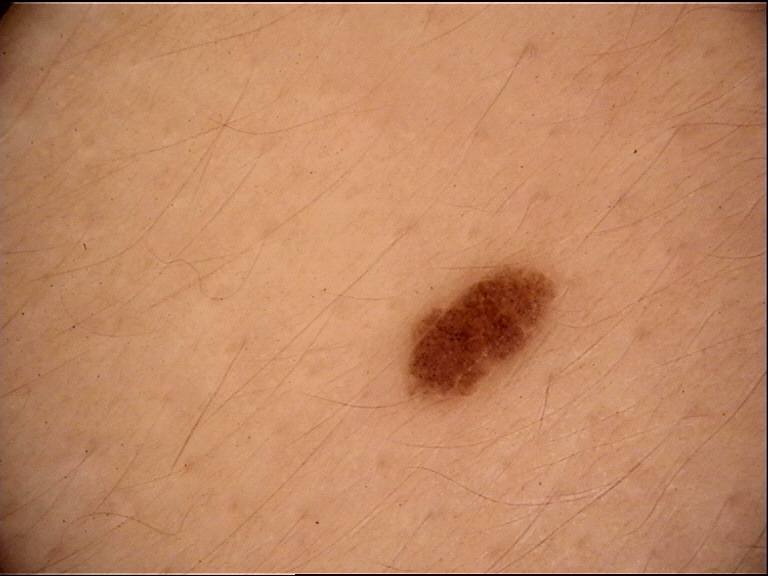Diagnosed as a compound nevus.